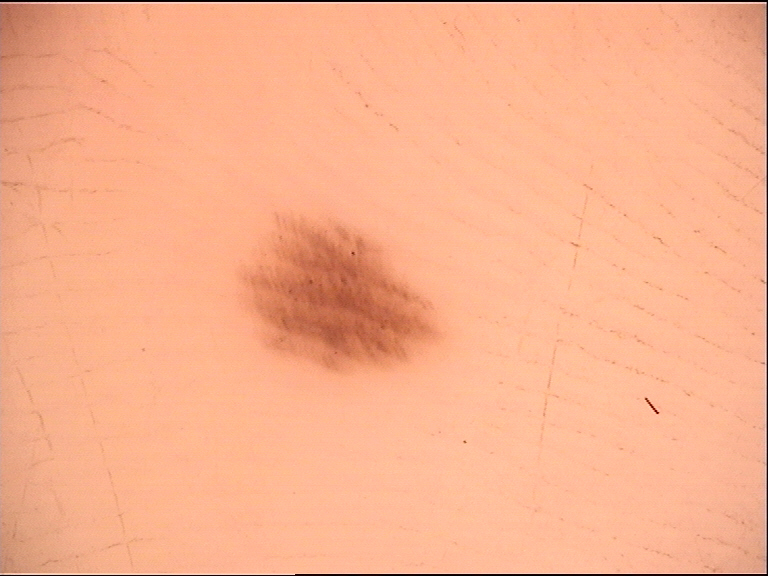diagnosis:
  name: acral dysplastic junctional nevus
  code: ajd
  malignancy: benign
  super_class: melanocytic
  confirmation: expert consensus